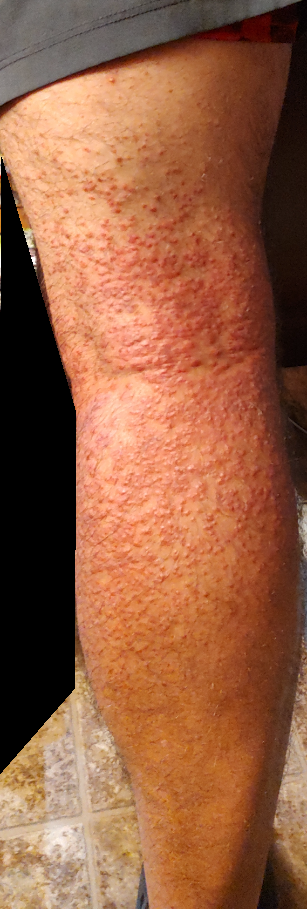The photograph was taken at a distance. Fitzpatrick III. The leading consideration is Lichen planus/lichenoid eruption.